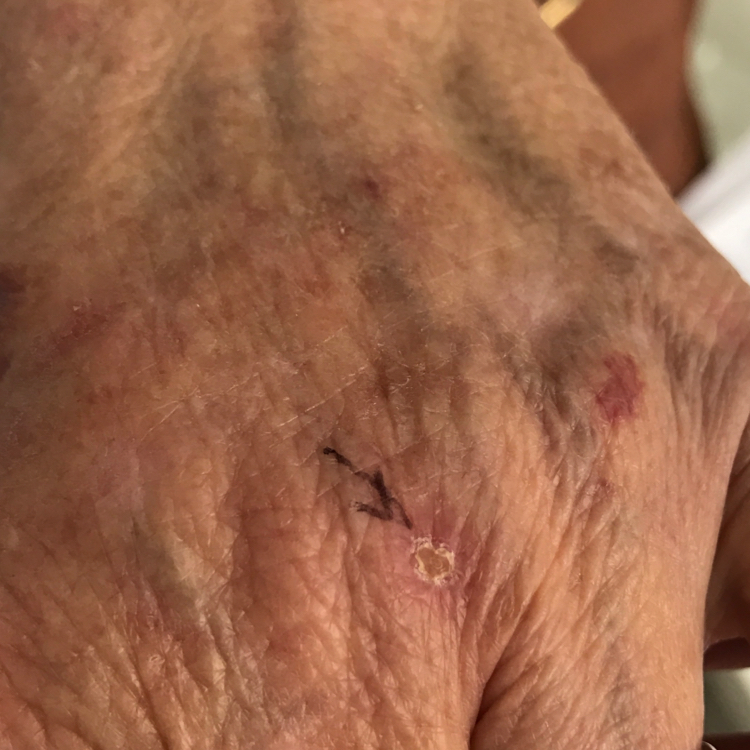image: smartphone clinical photo
patient:
  age: 57
symptoms:
  present:
    - pain
  absent:
    - elevation
    - itching
diagnosis:
  name: actinic keratosis
  code: ACK
  malignancy: indeterminate
  confirmation: clinical consensus